A dermoscopic view of a skin lesion. The subject is a female aged around 35: 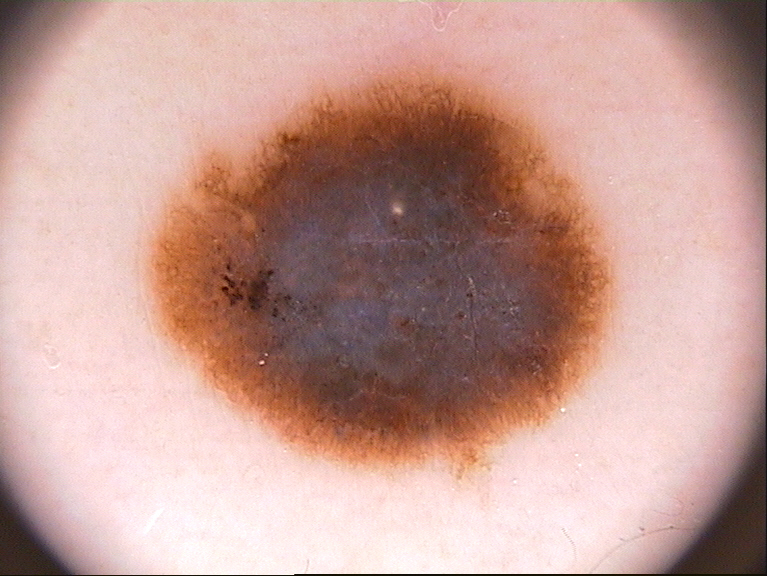Q: What dermoscopic features are present?
A: globules and pigment network; absent: milia-like cysts, streaks, and negative network
Q: Where is the lesion located?
A: x1=145, y1=51, x2=616, y2=471
Q: How much of the field does the lesion occupy?
A: ~32% of the field
Q: What is this lesion?
A: a melanoma, a skin cancer